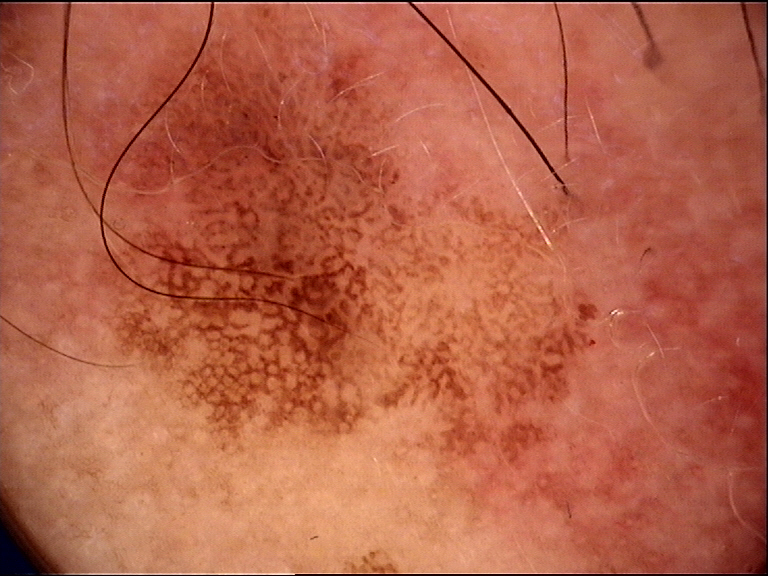A skin lesion imaged with a dermatoscope. The morphology is that of a keratinocytic lesion. Diagnosed as a benign lesion — a seborrheic keratosis.